A skin lesion imaged with a dermatoscope, a male subject aged around 25.
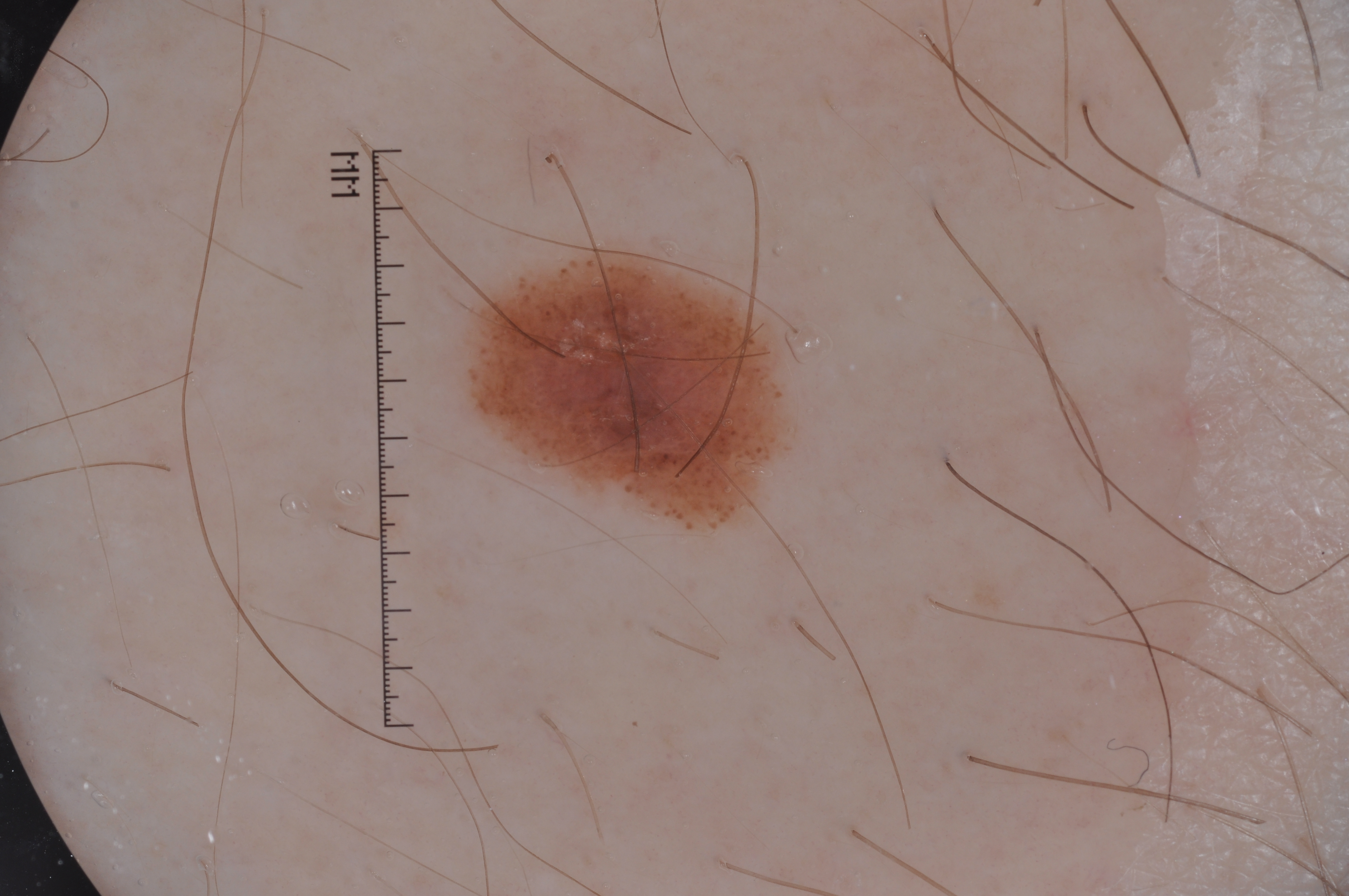dermoscopic findings = pigment network; absent: negative network, streaks, and milia-like cysts
lesion location = 474 252 780 525
impression = a melanocytic nevus, a benign lesion